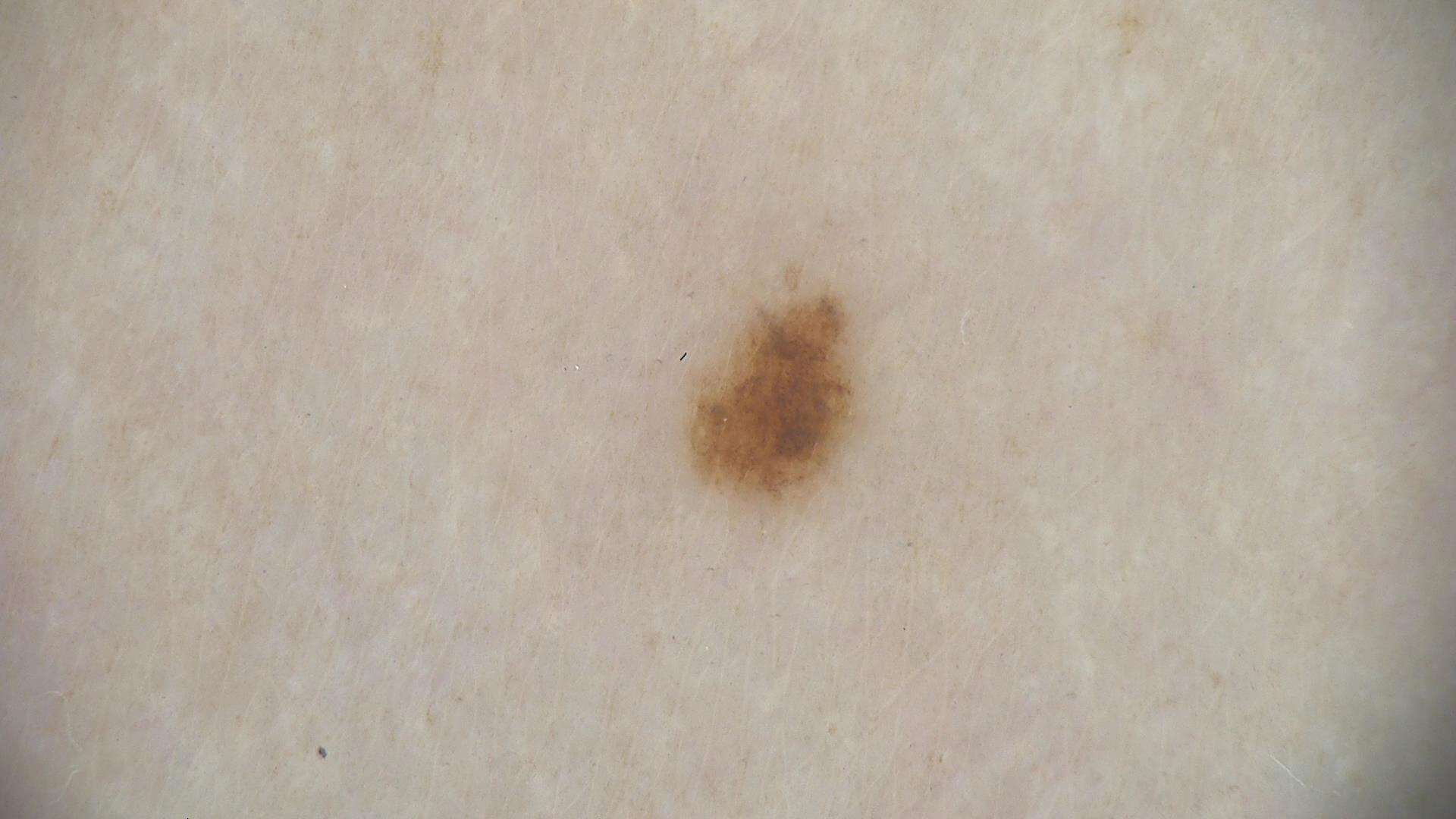The diagnosis was a dysplastic junctional nevus.